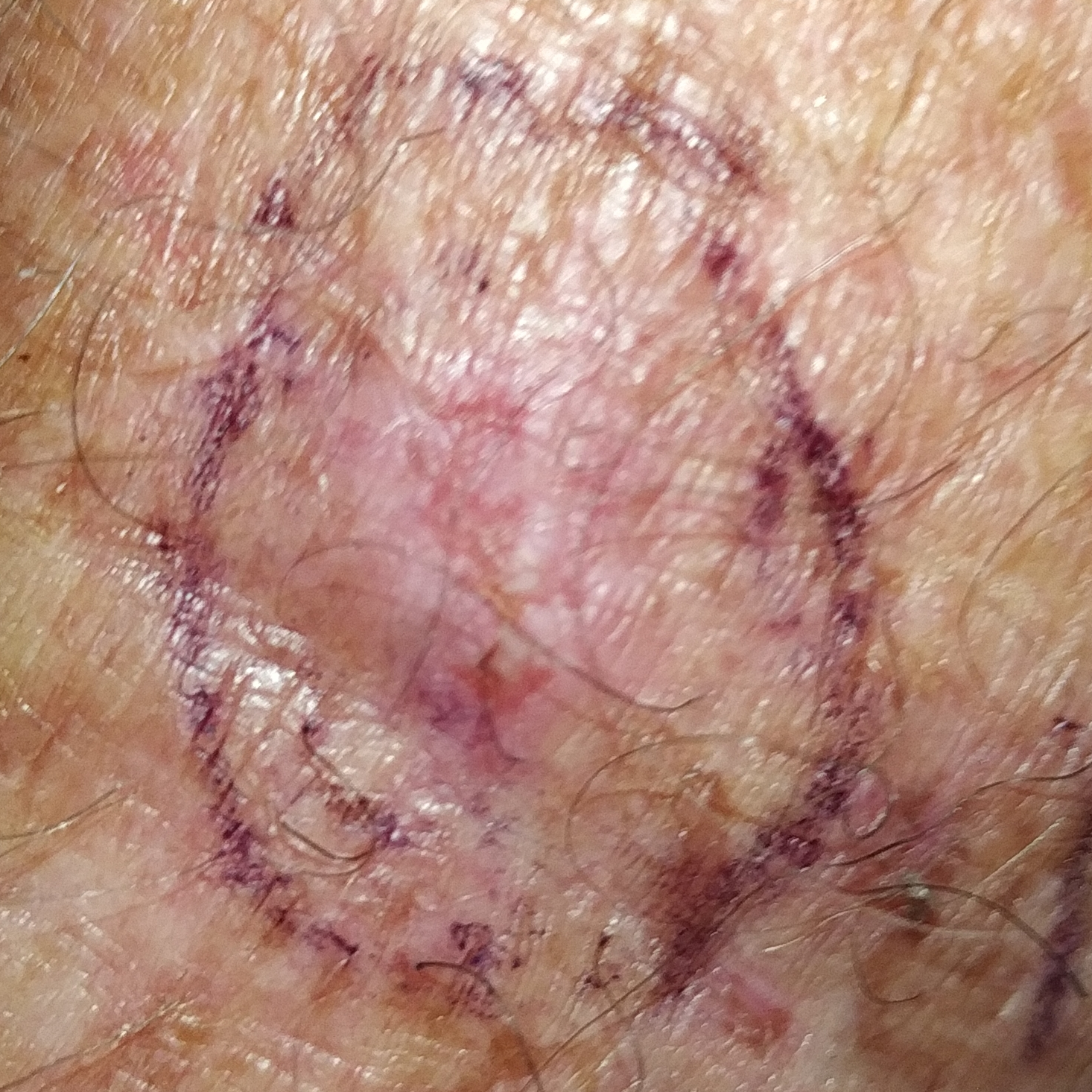Case summary:
A clinical photo of a skin lesion taken with a smartphone. A male subject in their 70s. The patient was assessed as skin type II. The chart notes prior malignancy (patient or family) and pesticide exposure. The lesion involves a forearm. The lesion measures 11 × 7 mm. By the patient's account, the lesion is elevated, has changed, and has grown, but does not hurt.
Conclusion:
Histopathologically confirmed as a squamous cell carcinoma.